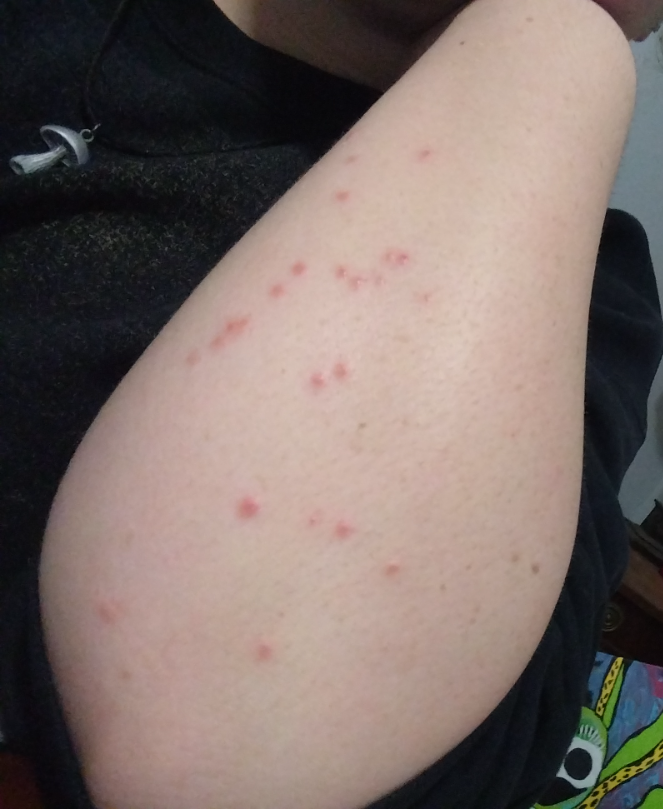The subject is a female aged 18–29.
The patient described the issue as skin that appeared healthy to them.
The lesion is associated with burning, itching and pain.
No relevant systemic symptoms.
The photograph was taken at an angle.
The contributor reports the lesion is raised or bumpy.
The affected area is the back of the hand, leg and arm.
Reported duration is less than one week.
Reviewed remotely by one dermatologist: the leading consideration is Insect Bite; also consider Eczema; possibly Molluscum Contagiosum.